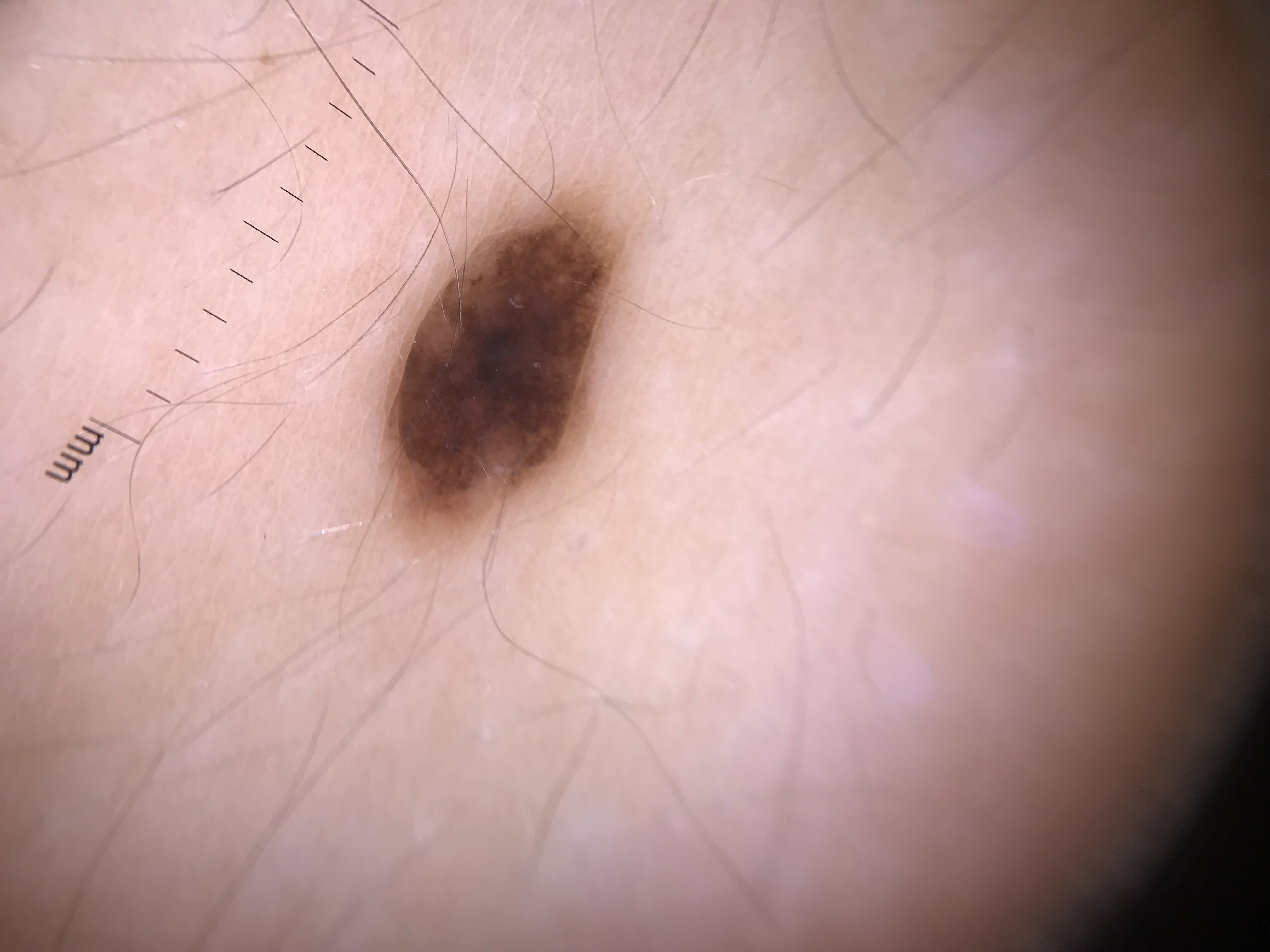Findings: A skin lesion imaged with a dermatoscope. Impression: Diagnosed as a banal lesion — a compound nevus.